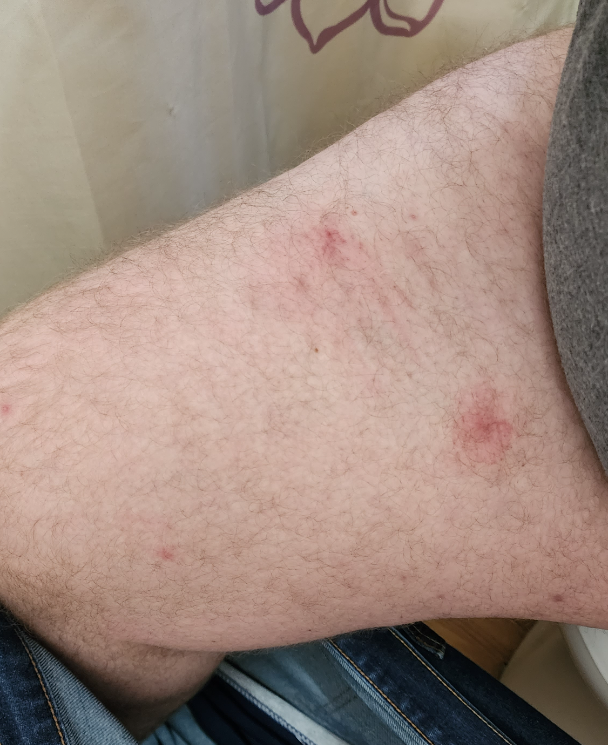{"assessment": "indeterminate from the photograph"}